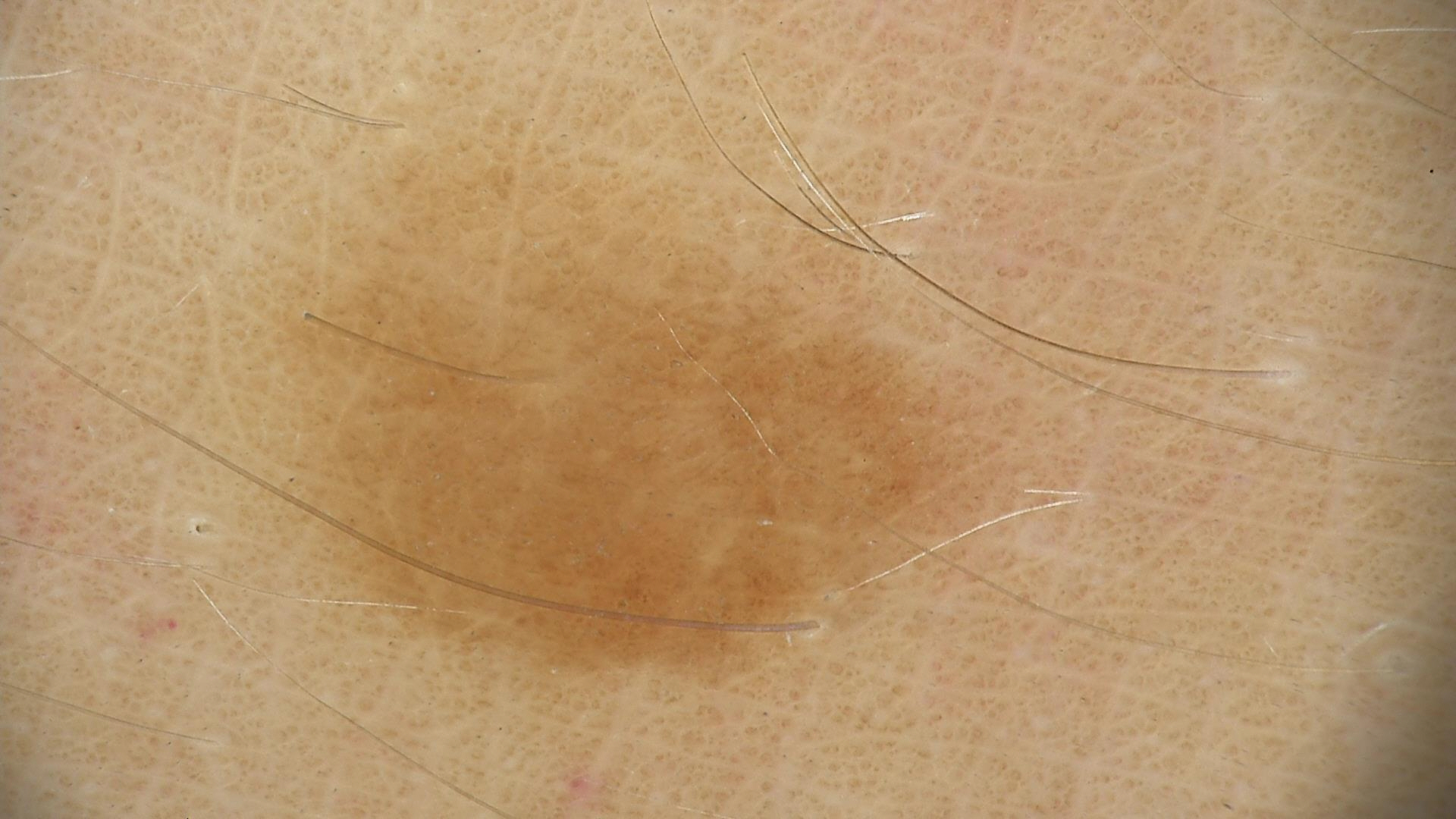Q: What was the diagnostic impression?
A: dysplastic junctional nevus (expert consensus)